A skin lesion imaged with a dermatoscope:
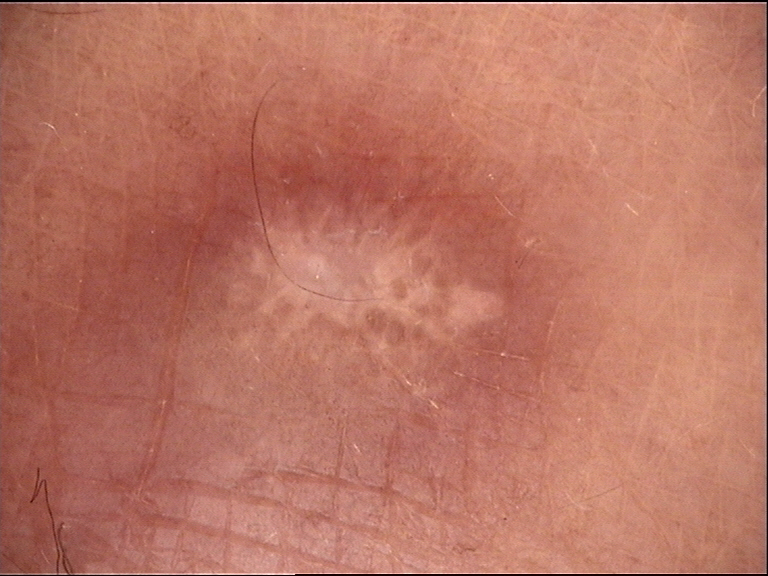Conclusion:
Labeled as a fibro-histiocytic, benign lesion — a dermatofibroma.